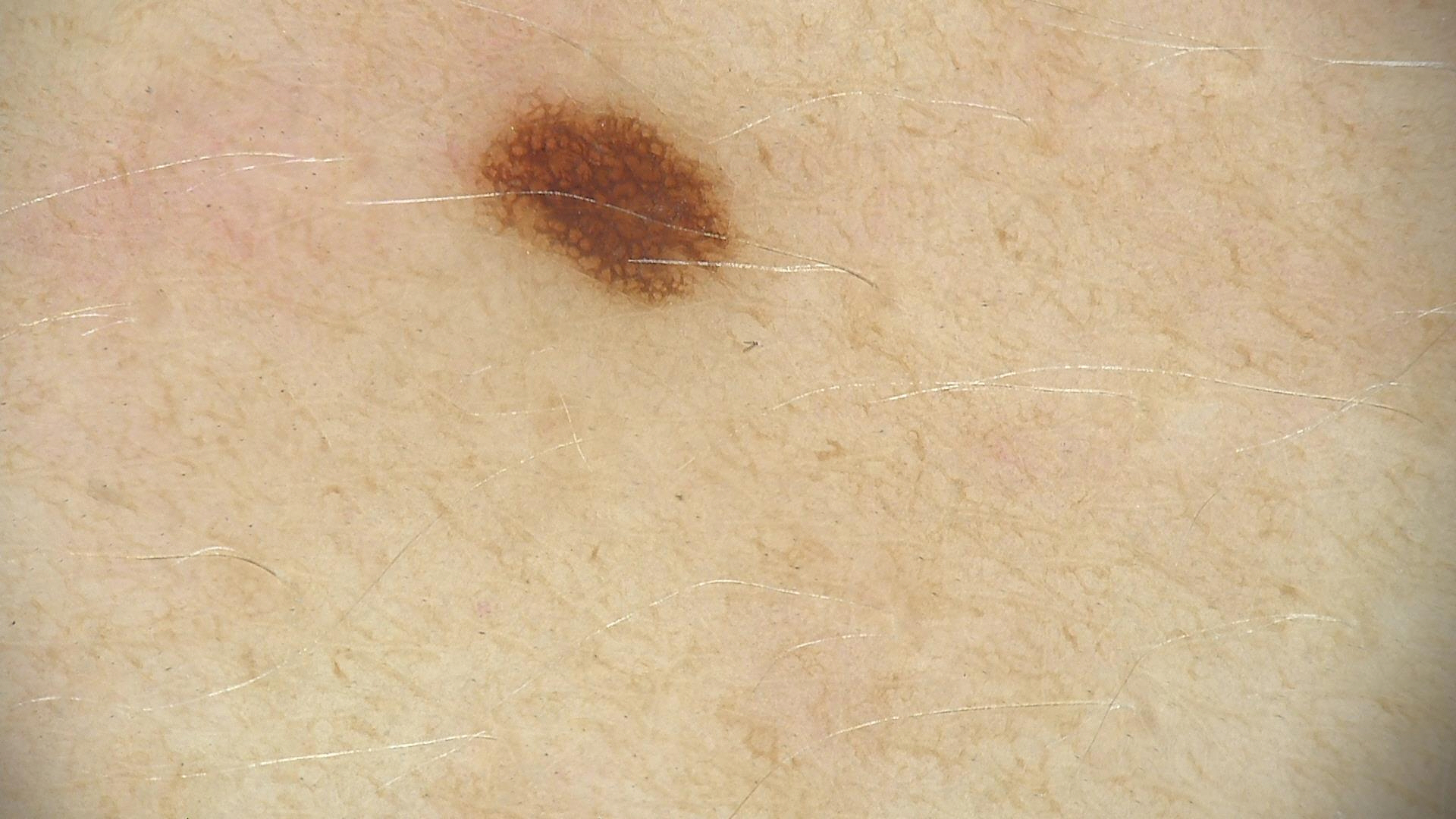Findings: A dermatoscopic image of a skin lesion. The architecture is that of a banal lesion. Conclusion: Diagnosed as a junctional nevus.